The patient was assessed as Fitzpatrick phototype II; contact-polarized dermoscopy of a skin lesion — 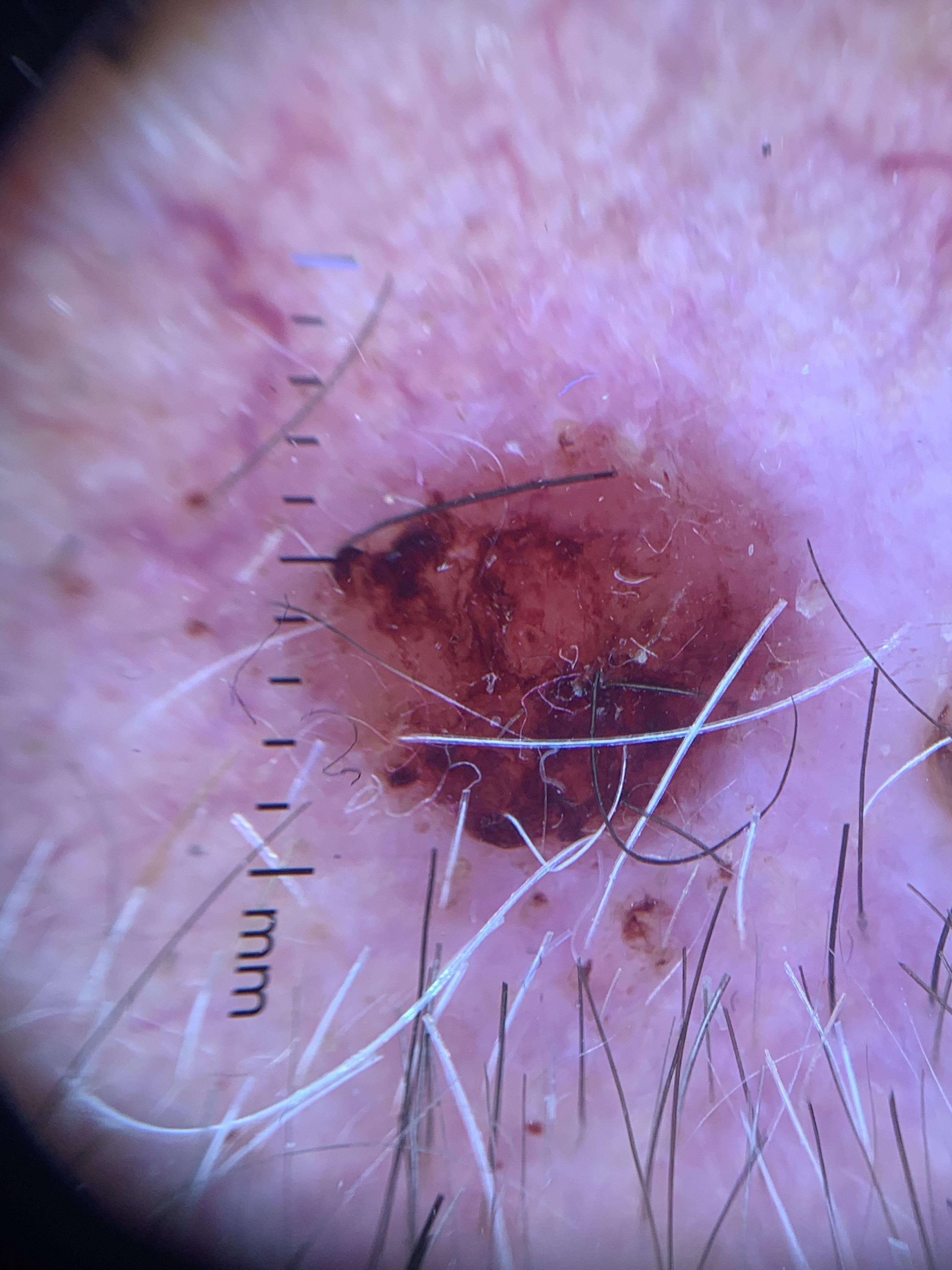Conclusion: Histopathologically confirmed as a malignancy — a squamous cell carcinoma.